A male patient, in their mid- to late 50s; a dermoscopy image of a single skin lesion: 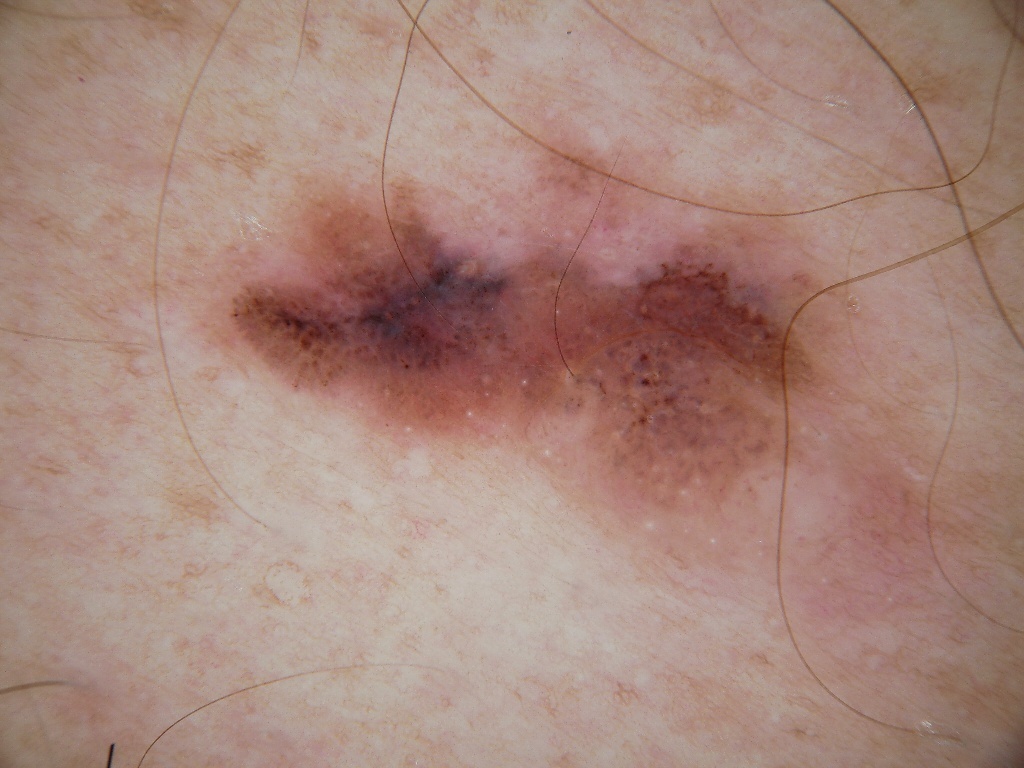Q: What is the lesion's bounding box?
A: box(202, 156, 987, 644)
Q: Lesion extent?
A: moderate
Q: What does dermoscopy show?
A: globules, negative network, and milia-like cysts
Q: What is this lesion?
A: a melanoma